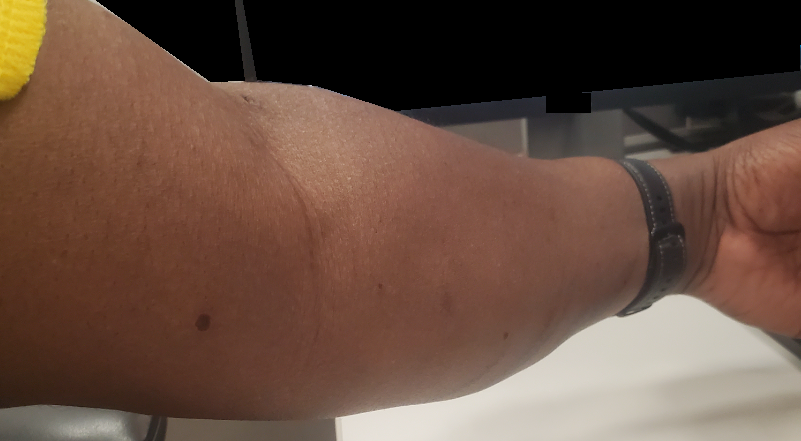No differential diagnosis could be assigned on photographic review.
The condition has been present for less than one week.
The patient considered this skin that appeared healthy to them.
This image was taken at a distance.
The affected area is the arm.
Symptoms reported: darkening.
No constitutional symptoms were reported.